Located on the arm · this is a close-up image · male subject, age 30–39:
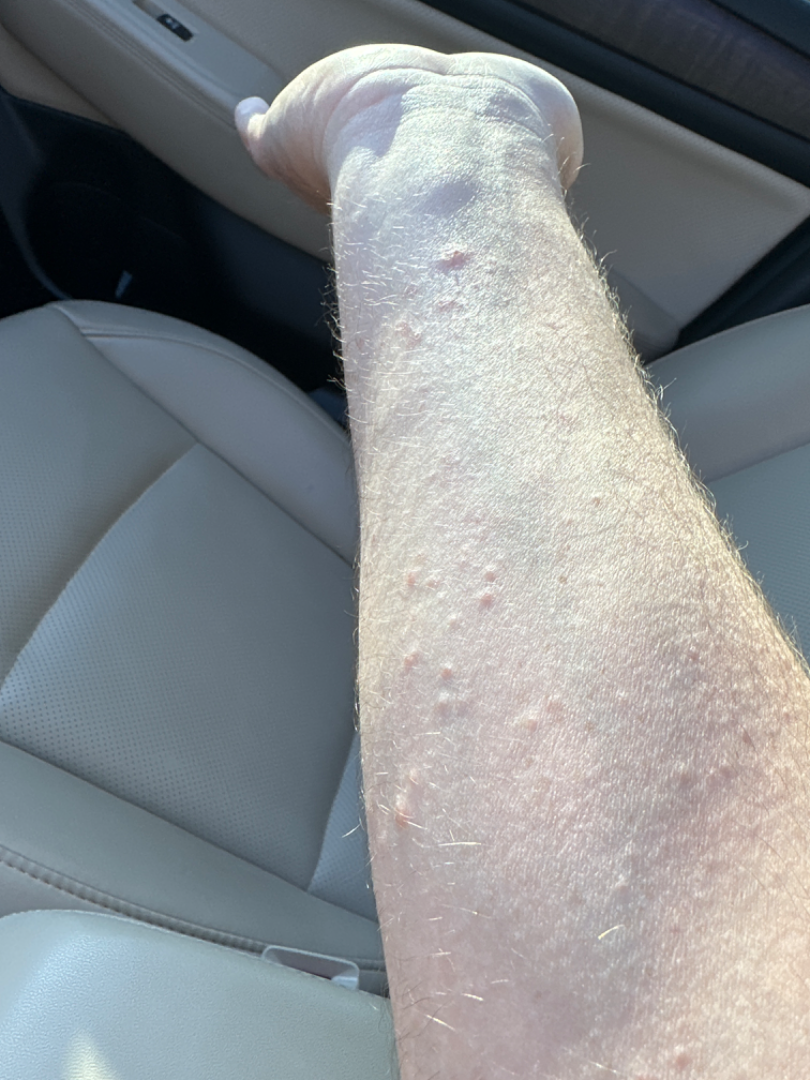- assessment: ungradable on photographic review